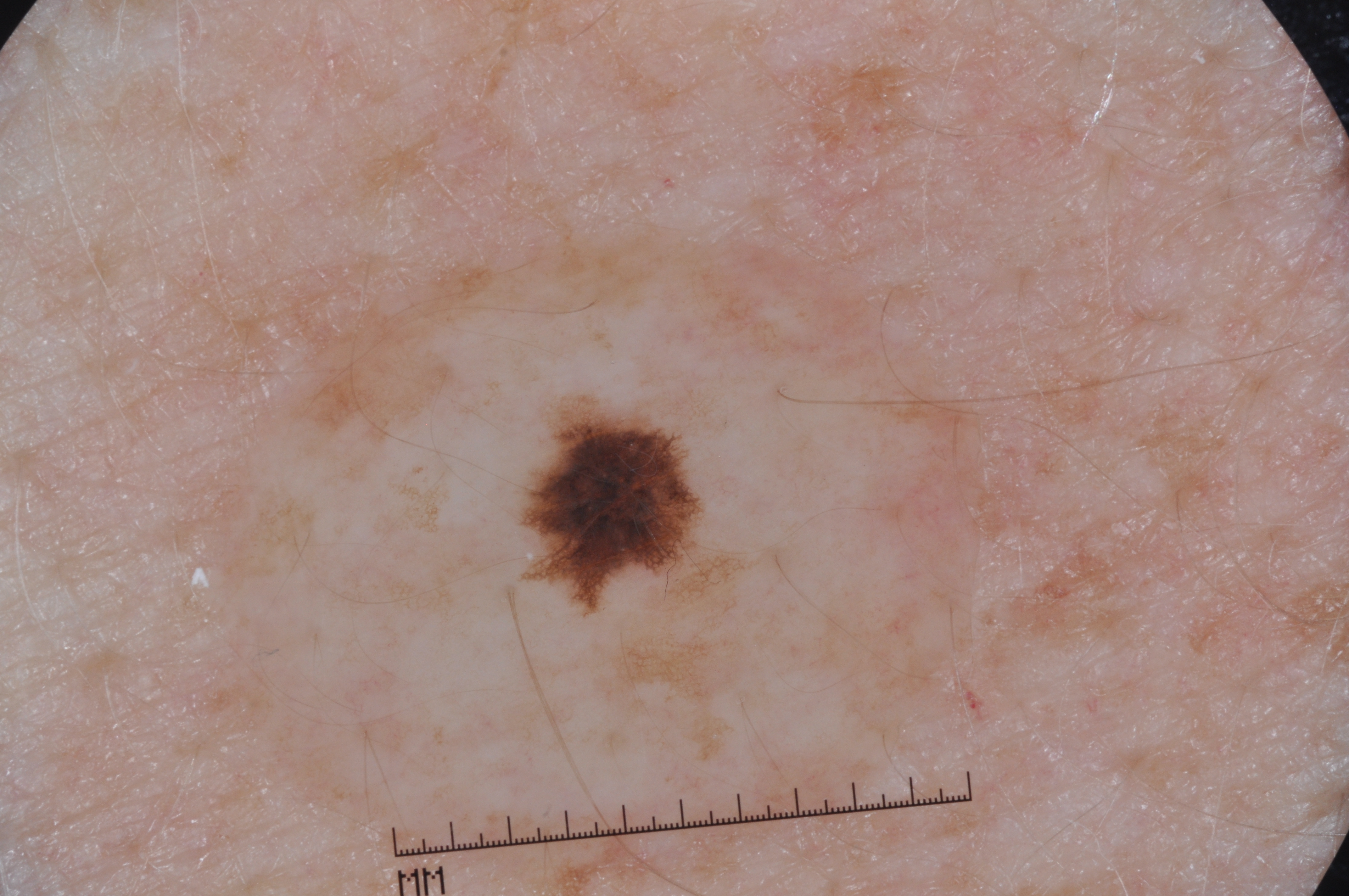Findings:
- modality — dermoscopy of a skin lesion
- location — <bbox>511, 390, 714, 619</bbox>
- diagnosis — a melanocytic nevus